Skin tone: Fitzpatrick phototype II. This image was taken at an angle. The lesion is described as flat. Present for less than one week. The affected area is the front of the torso, leg, head or neck, back of the torso and top or side of the foot:
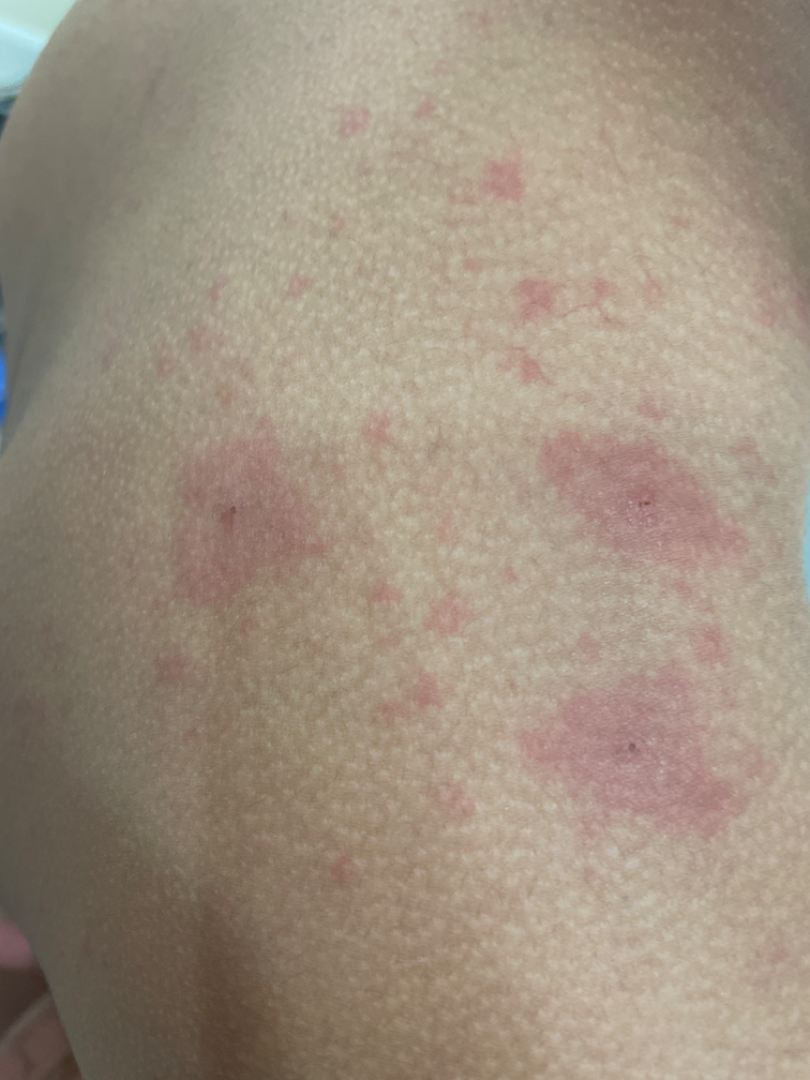Findings: The reviewing clinician's impression was: the differential is split between Eczema, Hypersensitivity and Allergic Contact Dermatitis.